A female subject aged 43 to 47 · dermoscopy of a skin lesion — 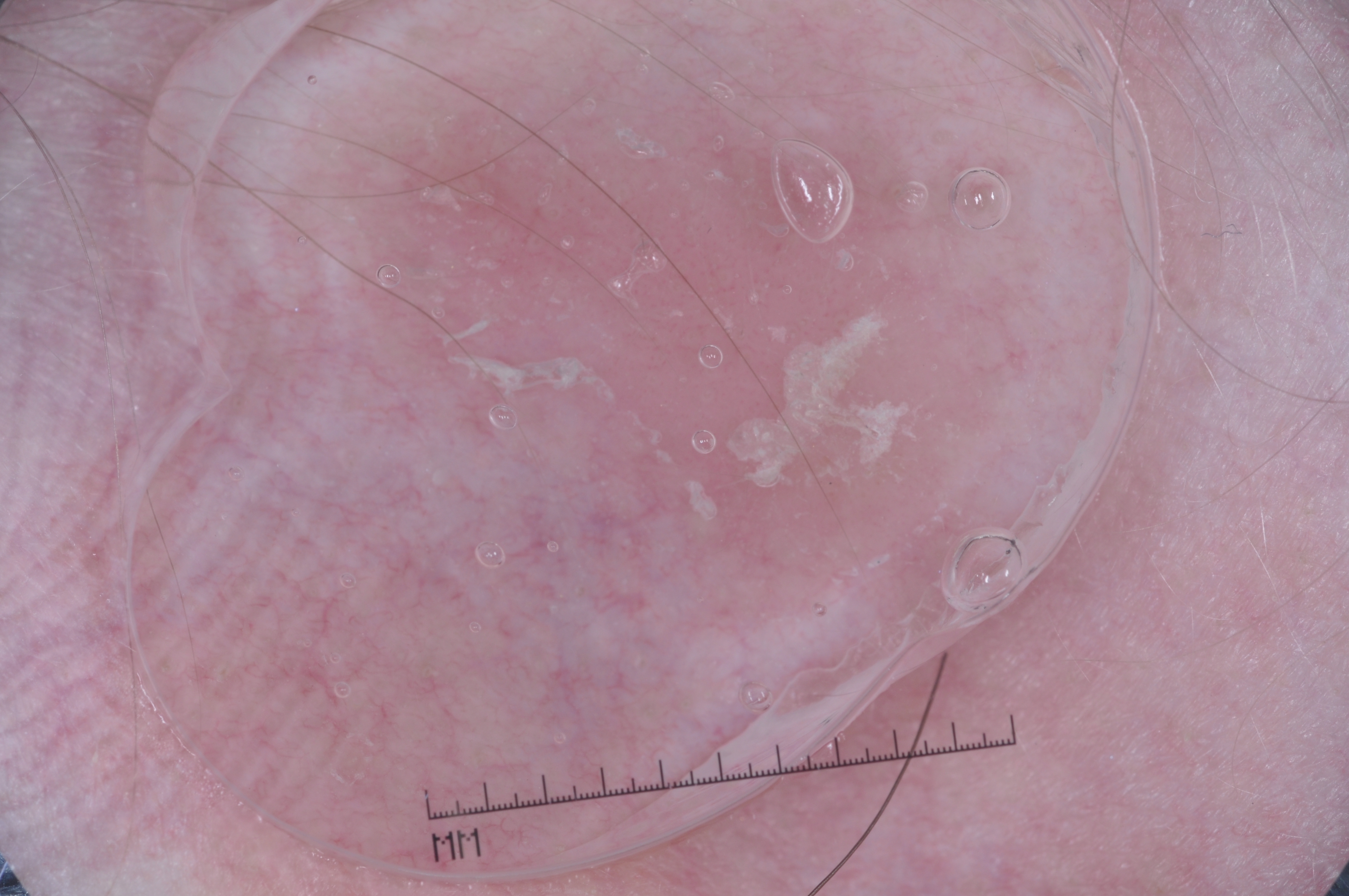Summary: The lesion spans bbox=[309, 35, 1053, 670]. The lesion takes up about 28% of the image. Dermoscopy demonstrates no negative network, streaks, pigment network, or milia-like cysts. Assessment: The clinical diagnosis was a seborrheic keratosis, a non-melanocytic (keratinocytic) lesion.